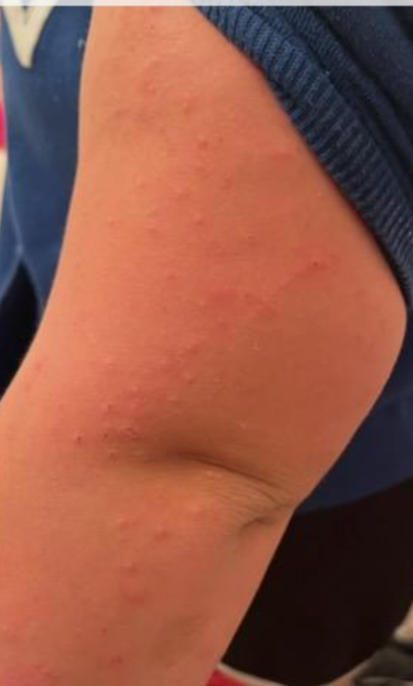differential: consistent with Eczema.